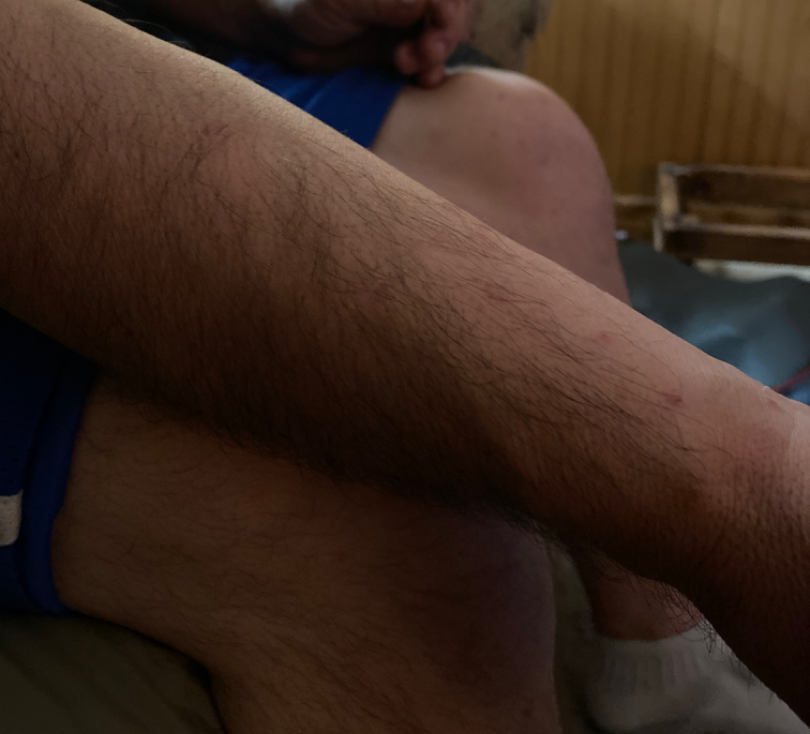Q: Could the case be diagnosed?
A: indeterminate from the photograph